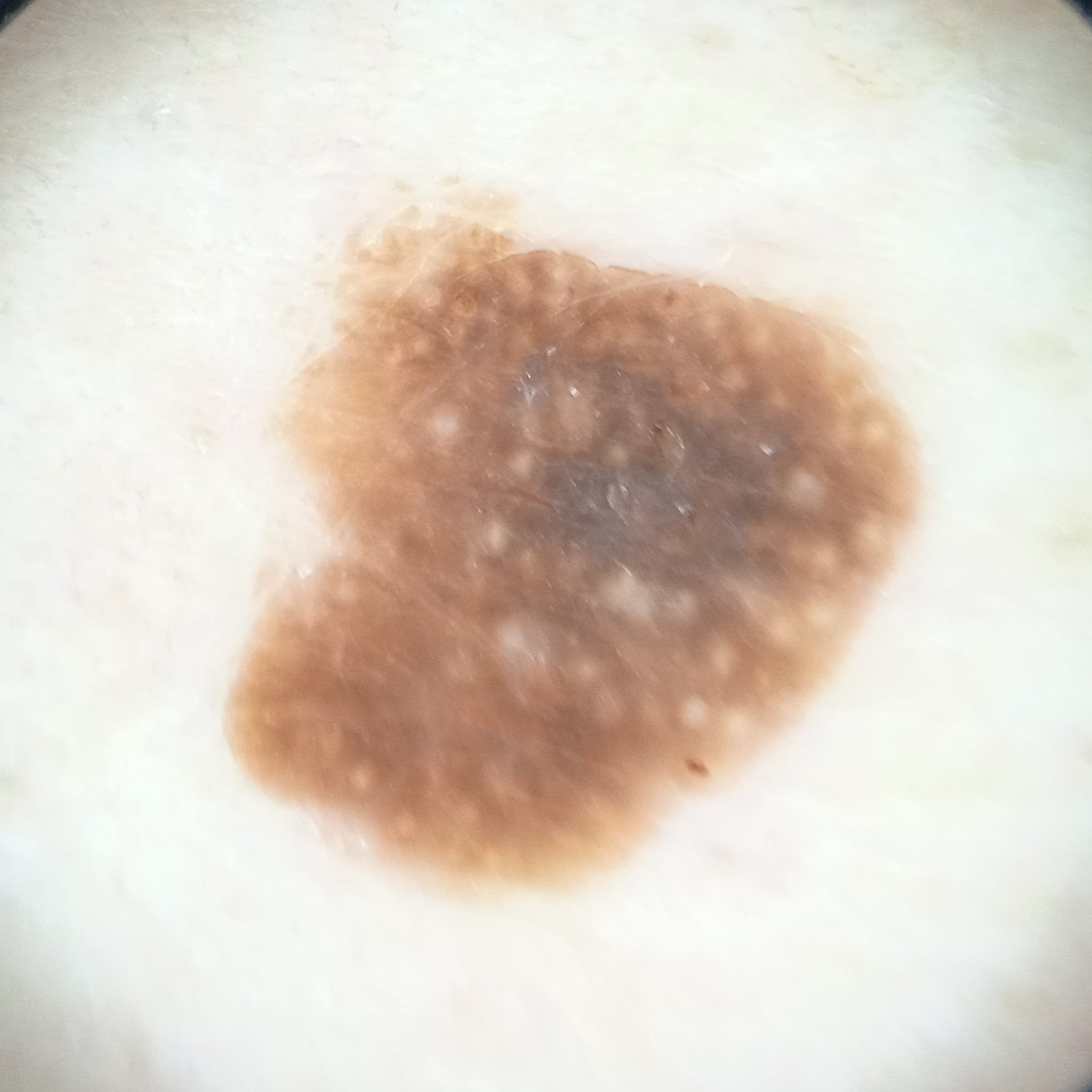The patient reports a personal history of skin cancer, a personal history of cancer, and no family history of skin cancer. Acquired for a research image collection, with no referral diagnosis. Few moles overall by the patient's own estimate. The patient says their skin reddens with sun exposure. A male patient age 76. The lesion measures approximately 8.6 mm. The lesion was assessed as a seborrheic keratosis.